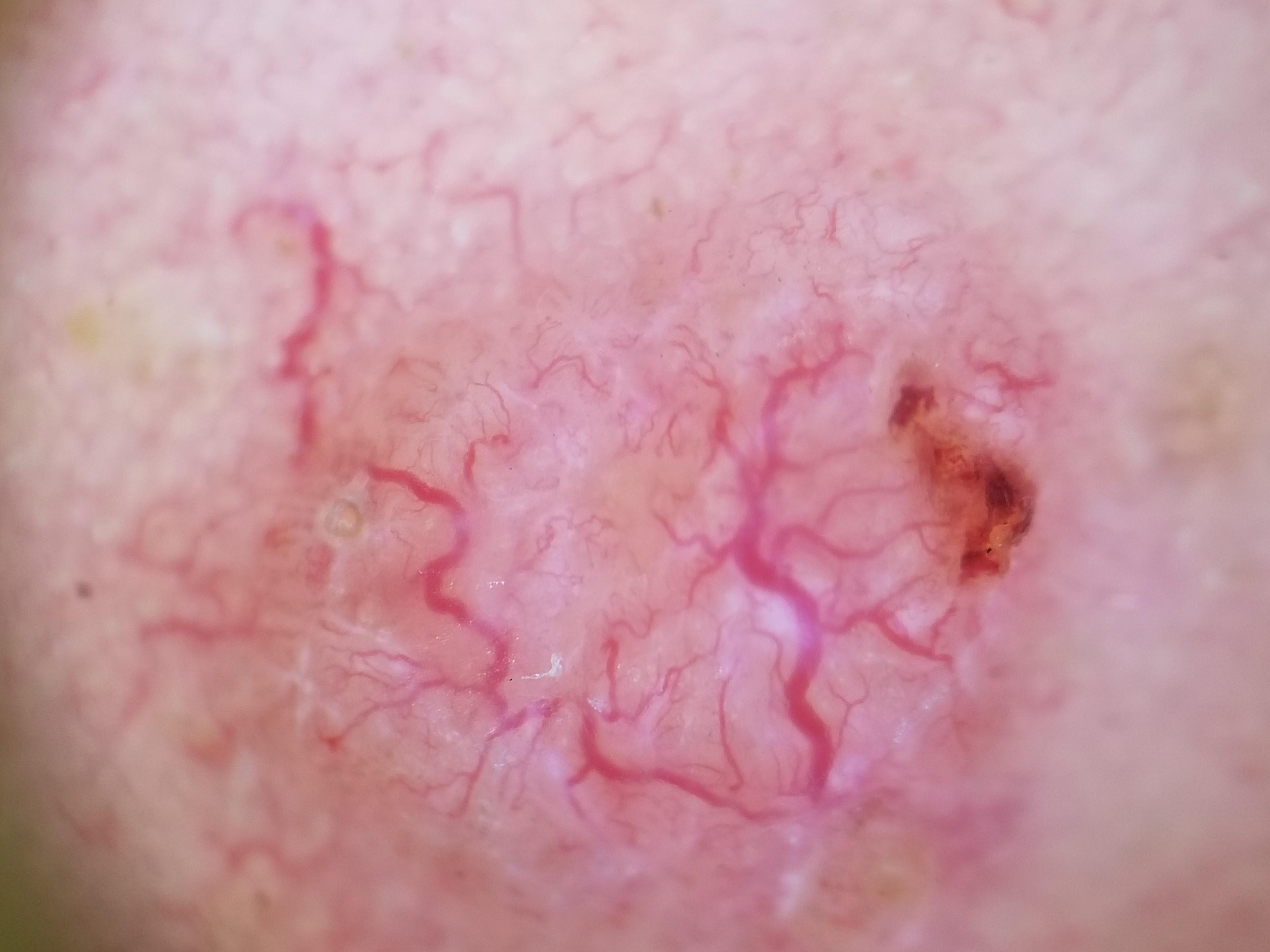{
  "image": "contact-polarized dermoscopy",
  "patient": {
    "age_approx": 75,
    "sex": "male"
  },
  "skin_type": "II",
  "lesion_location": {
    "region": "the head or neck"
  },
  "diagnosis": {
    "name": "Basal cell carcinoma",
    "malignancy": "malignant",
    "confirmation": "histopathology",
    "lineage": "adnexal"
  }
}